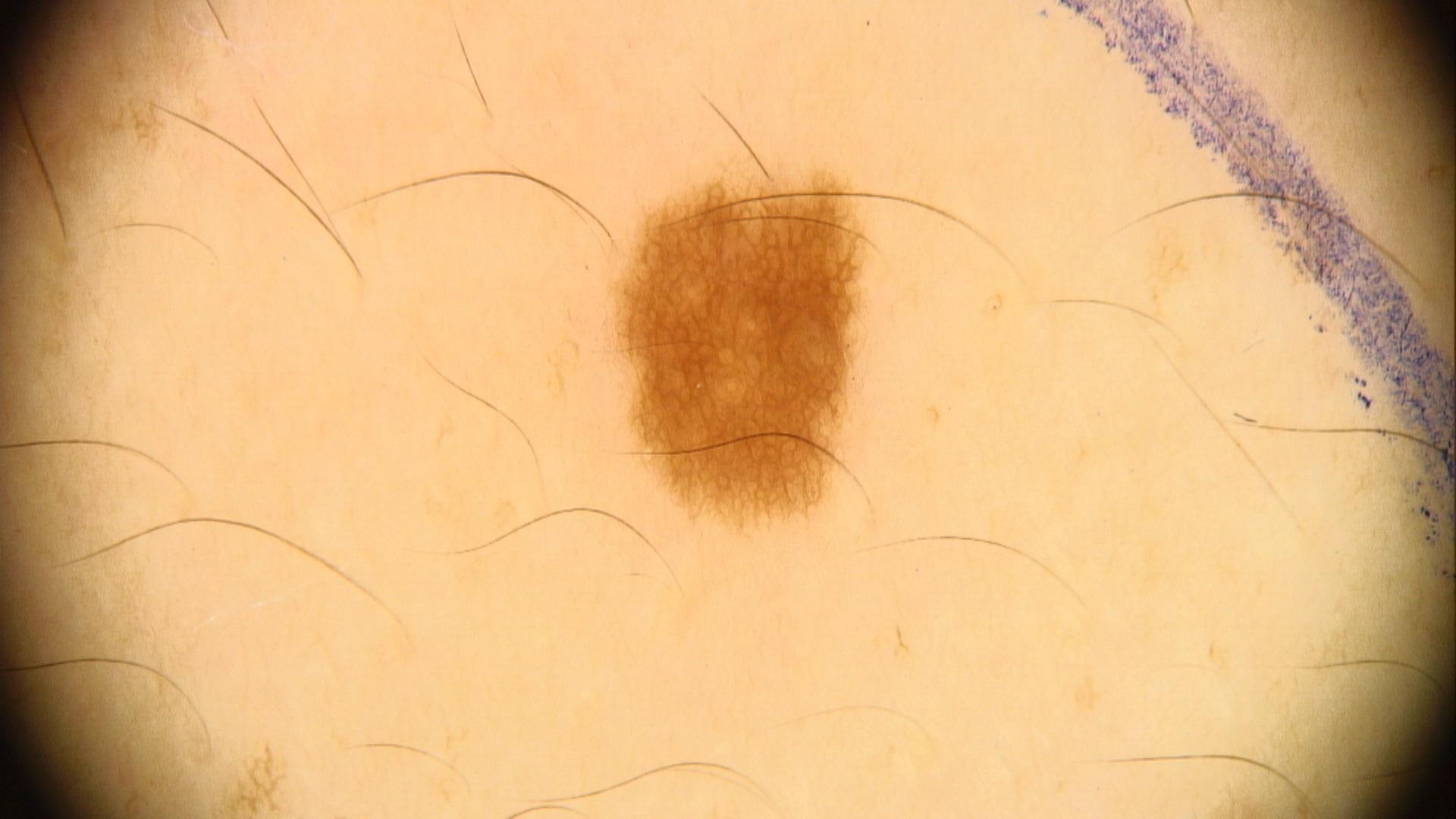Q: What are the patient's age and sex?
A: male, in their 40s
Q: What is the anatomic site?
A: the trunk
Q: What was the clinical impression?
A: Nevus